A male subject 72 years old. Acquired for a research image collection, with no referral diagnosis. A clinical close-up of a skin lesion. The patient describes having a moderate number of moles. The patient says their skin tans without first burning.
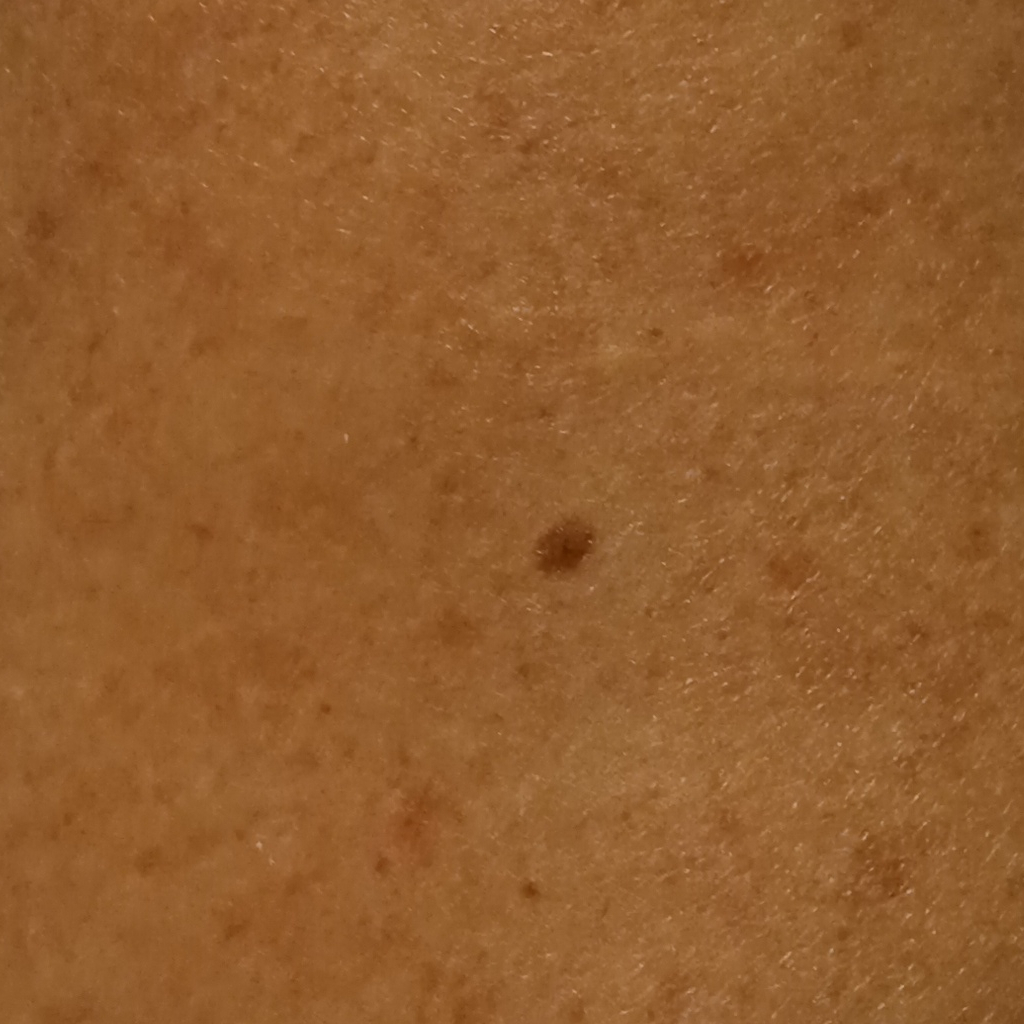Summary: Measuring roughly 3.7 mm. Assessment: The diagnostic impression was a melanocytic nevus.